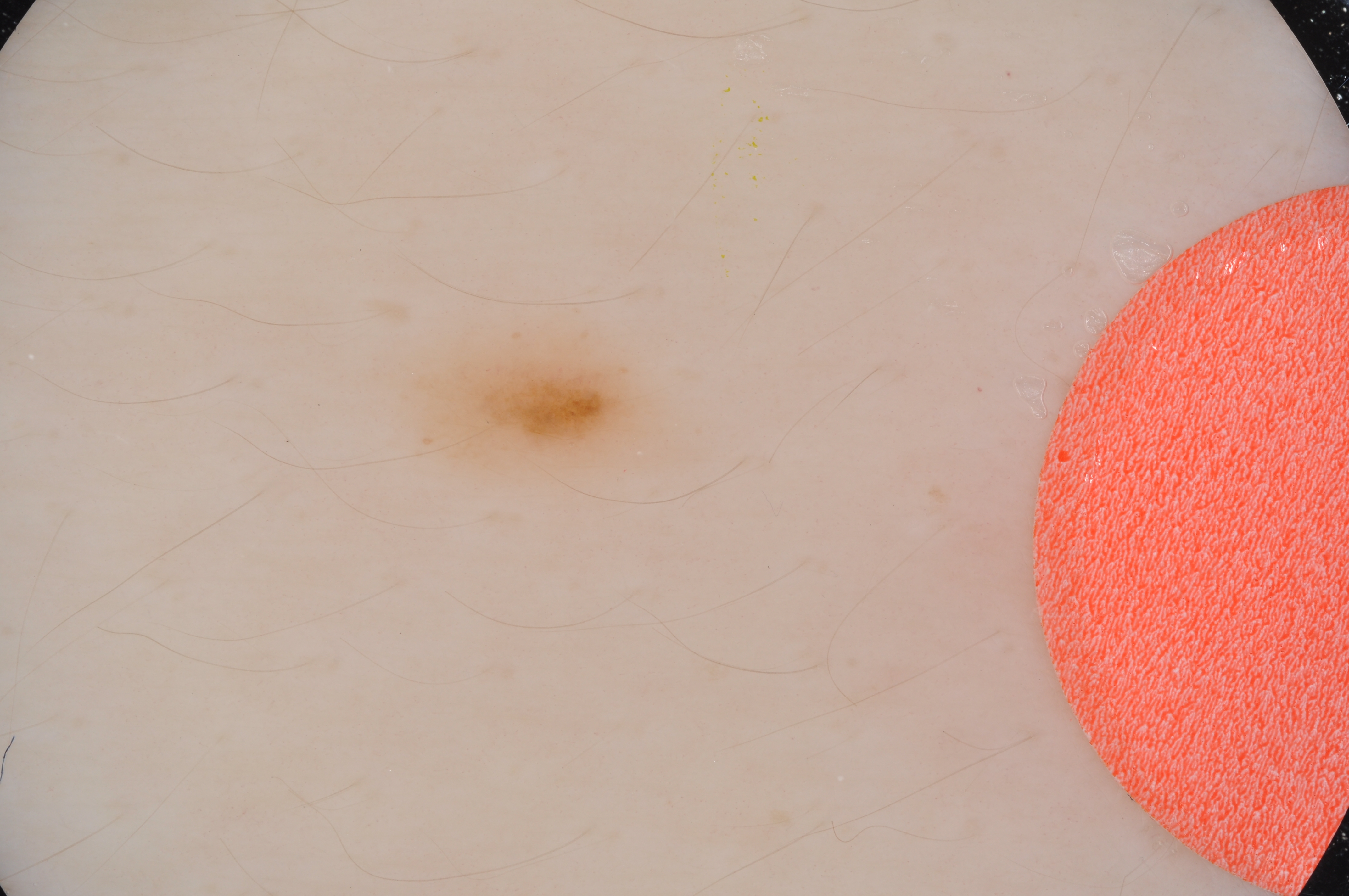A dermoscopic view of a skin lesion. The patient is a female aged approximately 15. In (x1, y1, x2, y2) order, the lesion occupies the region [391, 324, 711, 487]. The lesion is small relative to the field of view. Dermoscopic review identifies milia-like cysts. Clinically diagnosed as a melanocytic nevus, a benign lesion.